The photograph is a close-up of the affected area; located on the arm, head or neck and back of the hand; self-categorized by the patient as a rash; texture is reported as raised or bumpy; the patient reported no relevant symptoms from the lesion; present for one to four weeks — 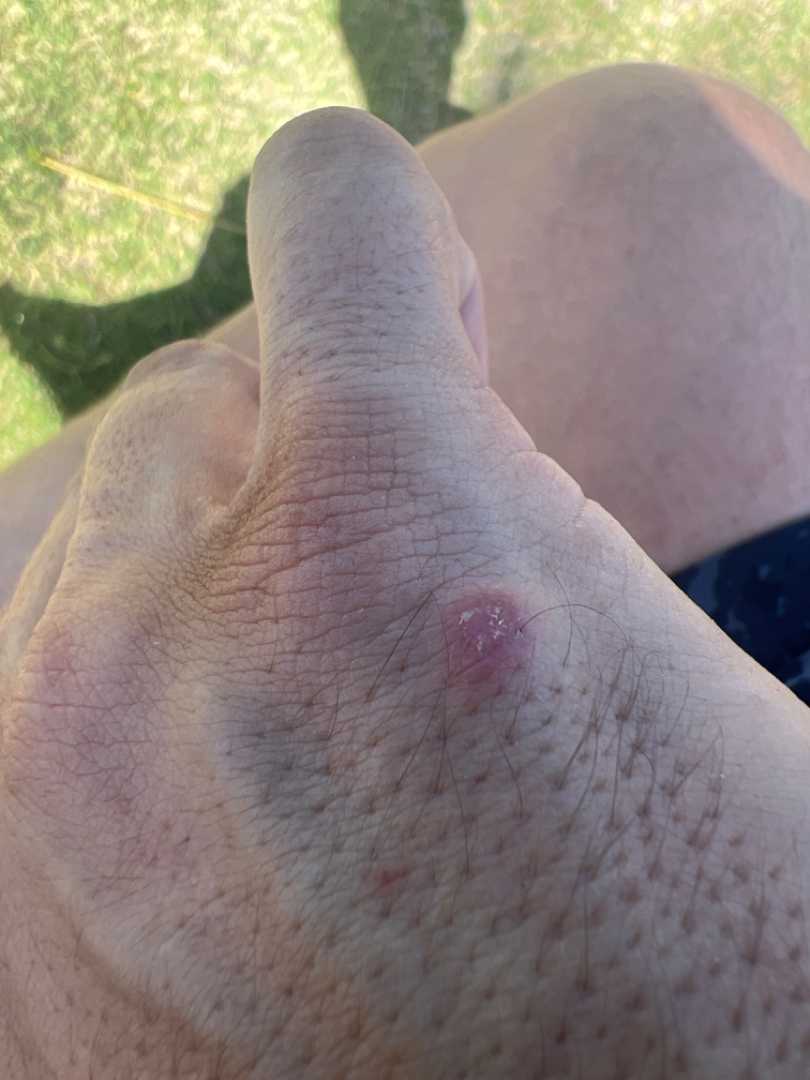– assessment · a single dermatologist reviewed the case: most likely Actinic Keratosis; also raised was Prurigo nodularis